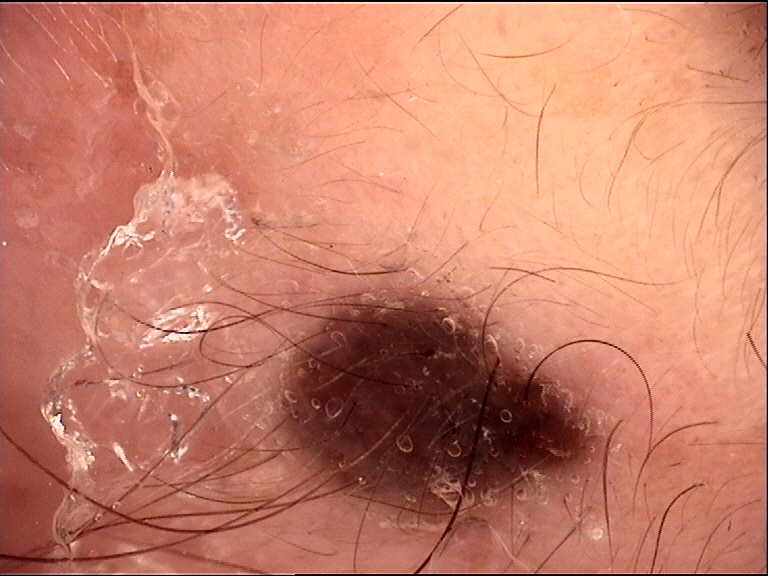A dermatoscopic image of a skin lesion. Classified as a banal lesion — a compound nevus.